The patient reports the condition has been present for about one day · the contributor is 40–49, female · symptoms reported: bothersome appearance · the head or neck is involved · the photograph is a close-up of the affected area · Fitzpatrick skin type III · the patient reports associated mouth sores · texture is reported as raised or bumpy:
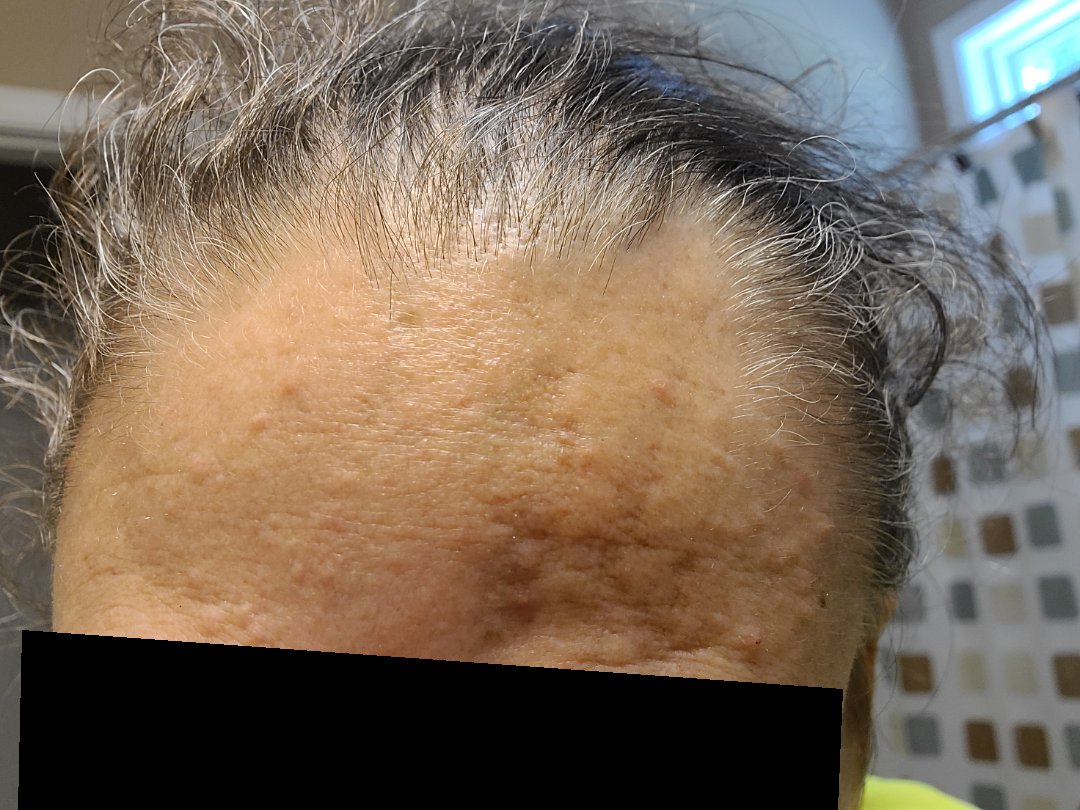Impression:
The skin condition could not be confidently assessed from this image.